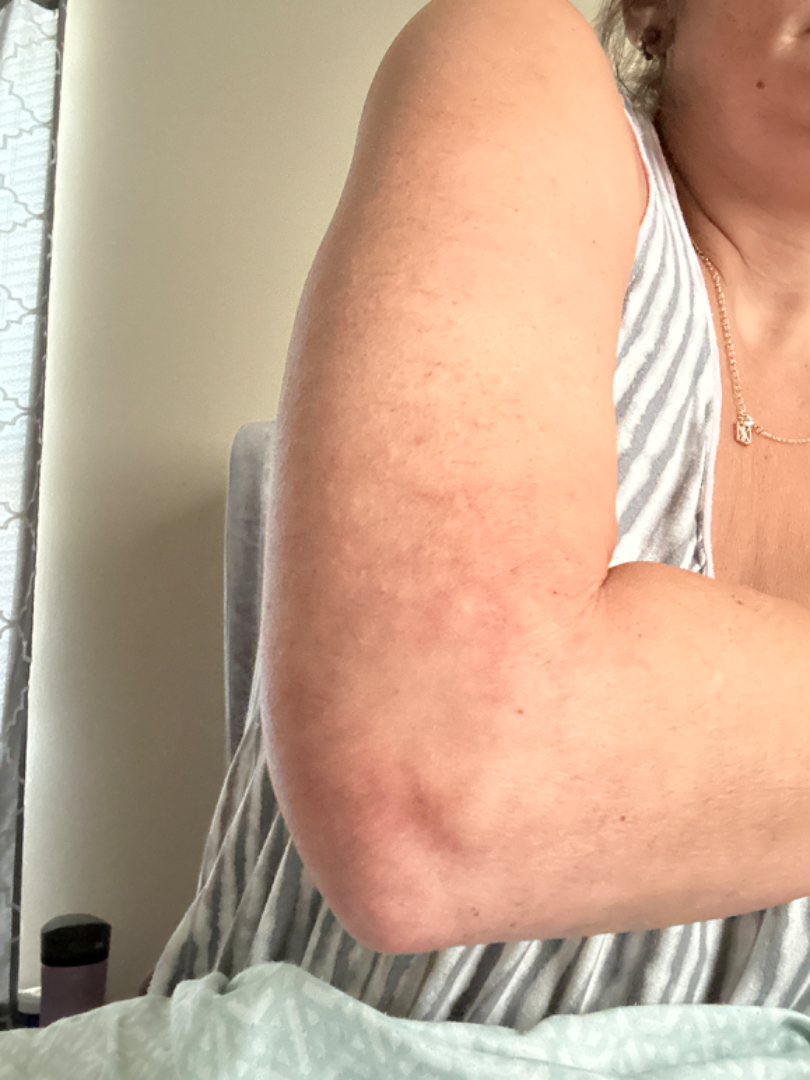Notes:
- dermatologist impression · in keeping with Erythema ab igne